A skin lesion imaged with a dermatoscope.
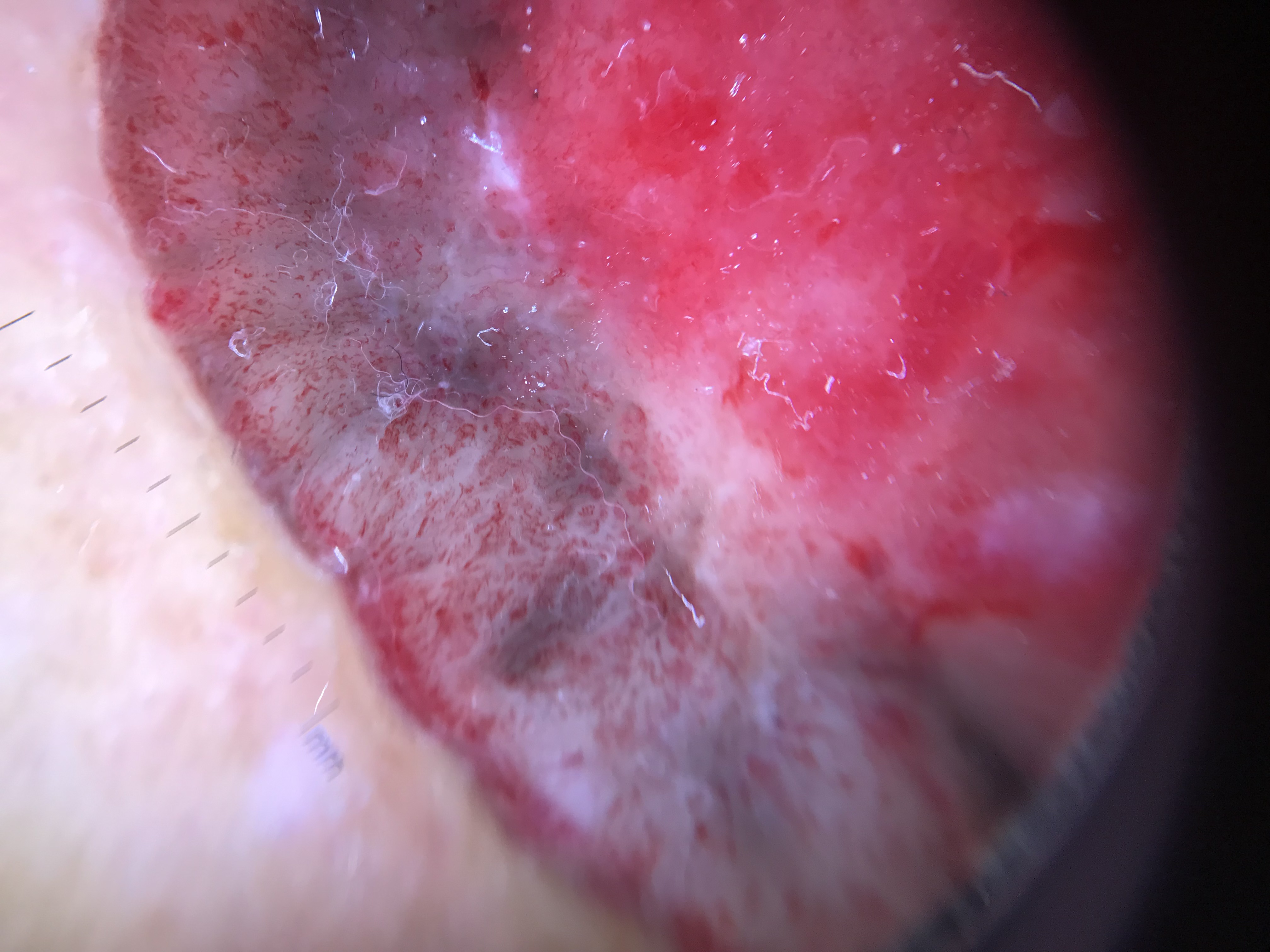pathology = basal cell carcinoma (biopsy-proven)